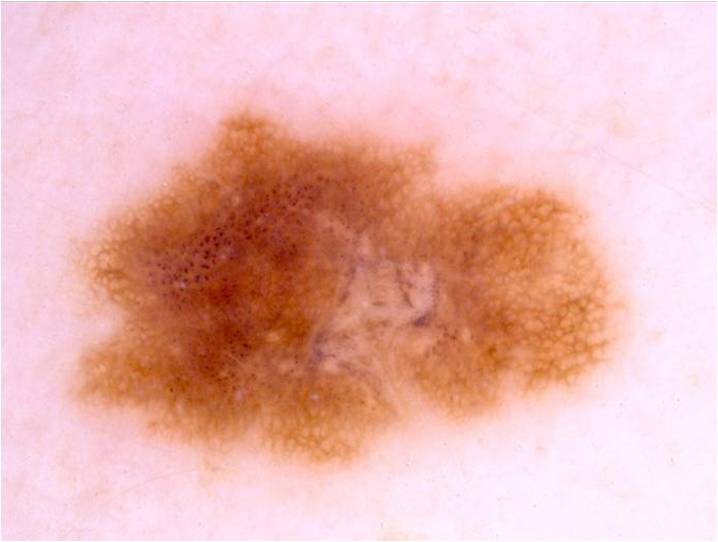Q: What are the patient's age and sex?
A: female, aged 28 to 32
Q: How was this image acquired?
A: dermoscopy
Q: Where is the lesion in the image?
A: [64,97,622,471]
Q: Lesion extent?
A: ~38% of the field
Q: What dermoscopic features are present?
A: pigment network and globules; absent: milia-like cysts, negative network, and streaks
Q: What is this lesion?
A: a melanocytic nevus